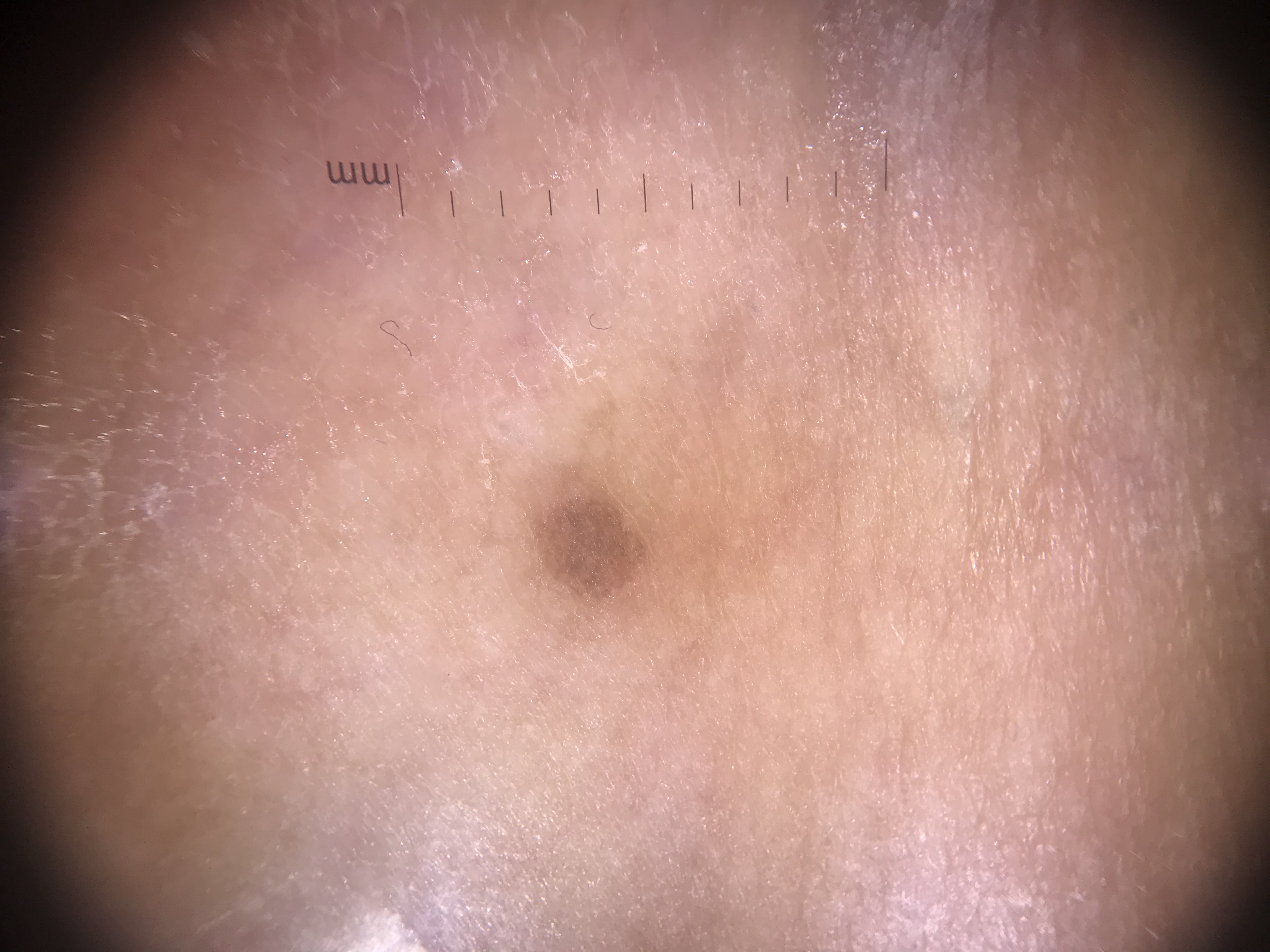image type = dermatoscopy; lesion type = banal; diagnosis = junctional nevus (expert consensus).